A dermoscopic image of a skin lesion:
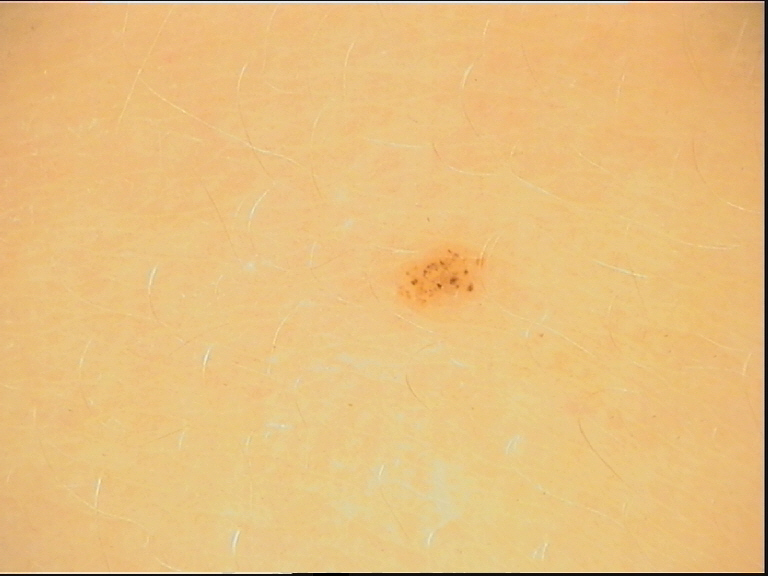| field | value |
|---|---|
| diagnostic label | dysplastic junctional nevus (expert consensus) |